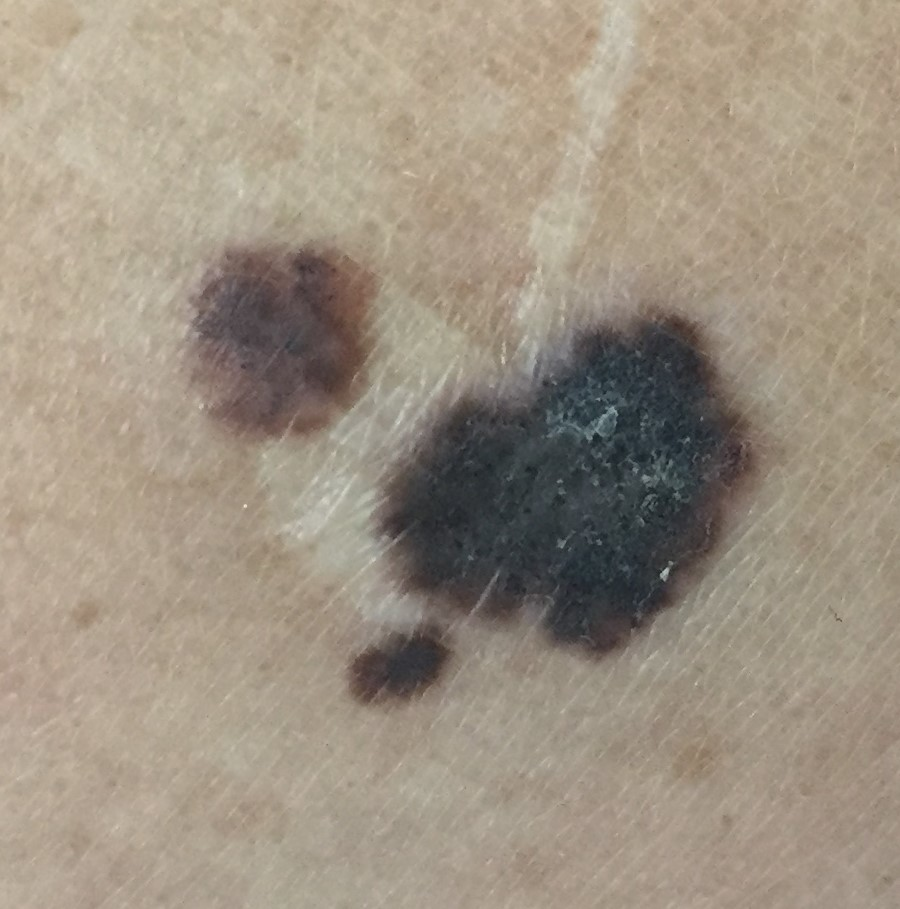Patient and lesion:
The chart notes no pesticide exposure. A female patient aged 49. The patient is Fitzpatrick II. The lesion is roughly 23 by 20 mm. Per patient report, the lesion has grown, has changed, and is elevated, but has not bled and does not hurt.
Conclusion:
The biopsy diagnosis was a malignancy — a melanoma.